The patient considered this a rash · the lesion involves the leg · reported lesion symptoms include itching and bothersome appearance · the patient is a female aged 40–49 · an image taken at an angle · no associated systemic symptoms reported · the contributor notes the condition has been present for more than one year · the contributor notes the lesion is fluid-filled and raised or bumpy: 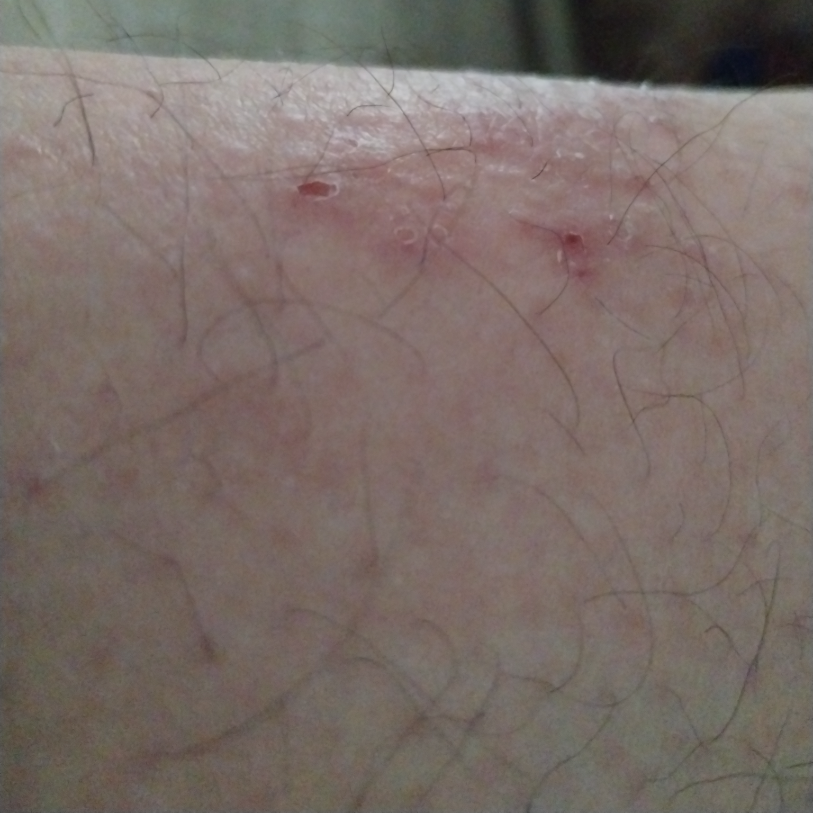assessment: indeterminate from the photograph.